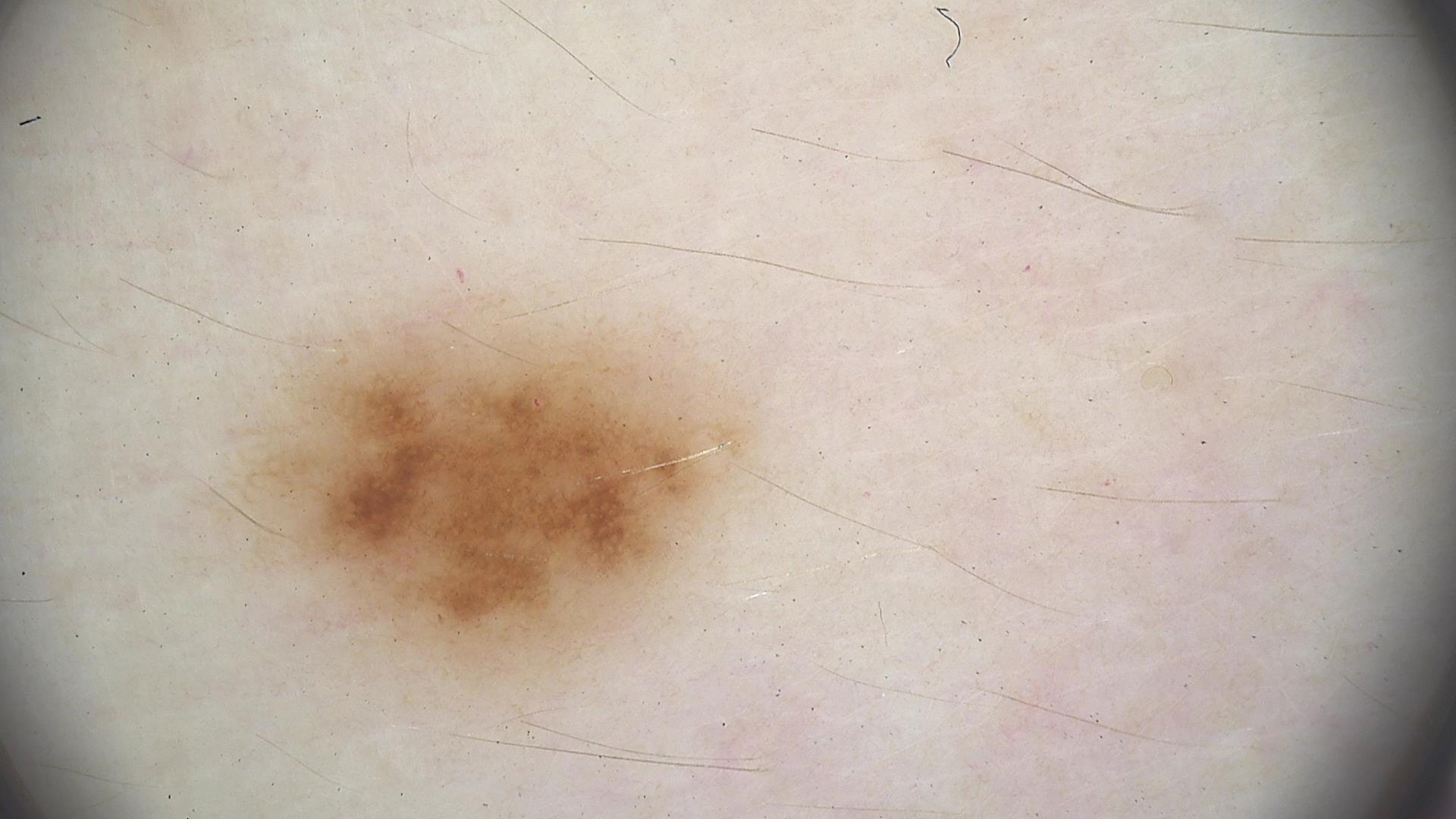Q: What is the imaging modality?
A: dermoscopy
Q: What is this lesion?
A: dysplastic junctional nevus (expert consensus)